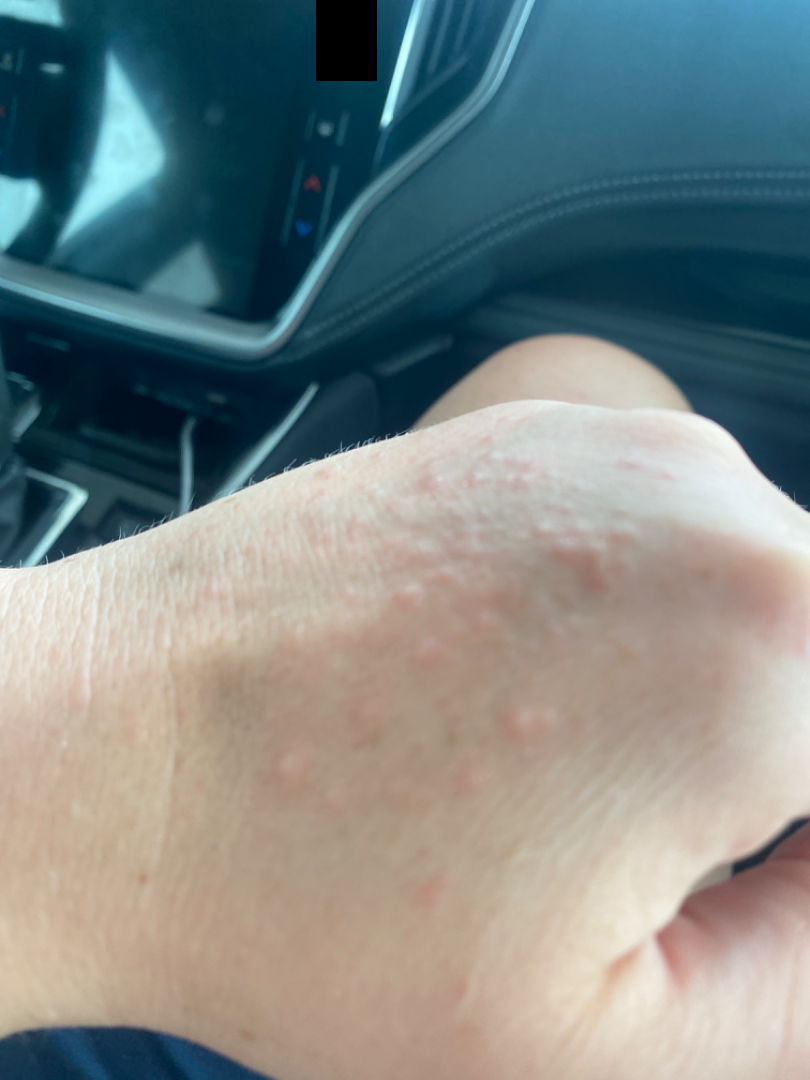  texture: raised or bumpy
  duration: less than one week
  shot_type: at an angle
  body_site:
    - back of the hand
    - leg
  differential:
    leading:
      - Photodermatitis
    considered:
      - Eczema
    unlikely:
      - Cutaneous lupus